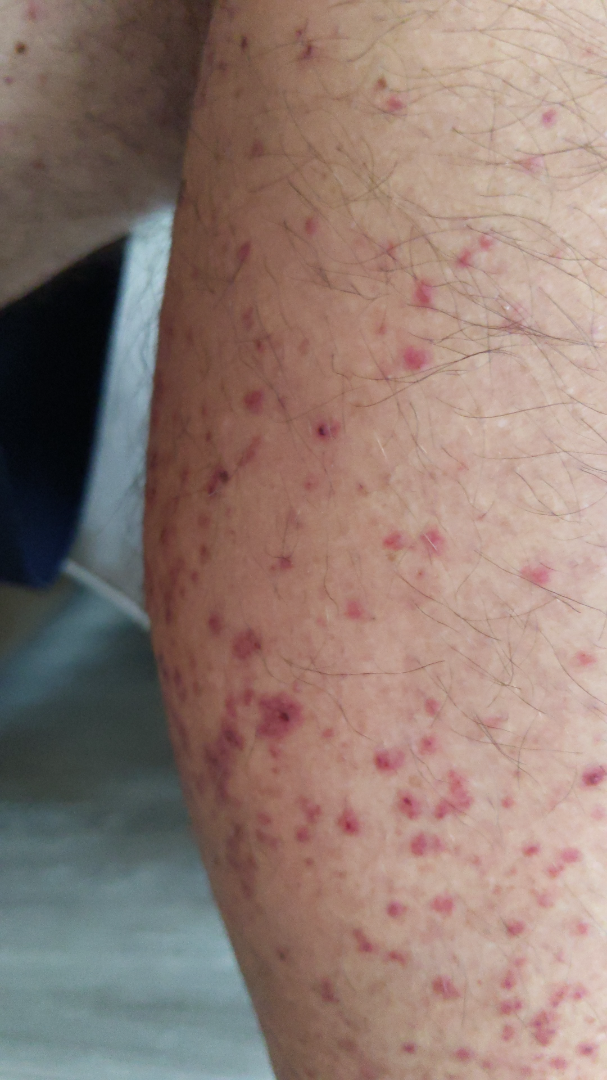Patient information:
Located on the leg, front of the torso, back of the torso and arm. The photo was captured at an angle.
Review:
On photographic review by a dermatologist, Leukocytoclastic Vasculitis (weight 1.00).